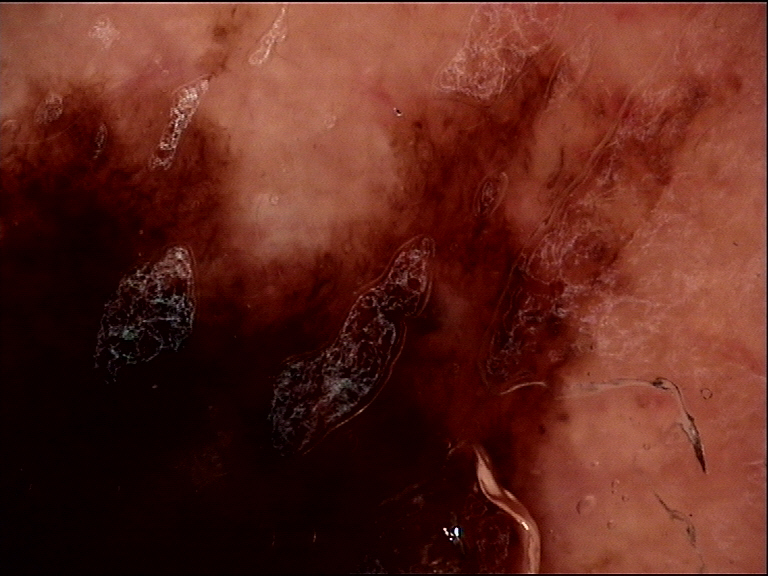{"image": "dermatoscopy", "diagnosis": {"name": "melanoma", "code": "mel", "malignancy": "malignant", "super_class": "melanocytic", "confirmation": "histopathology"}}